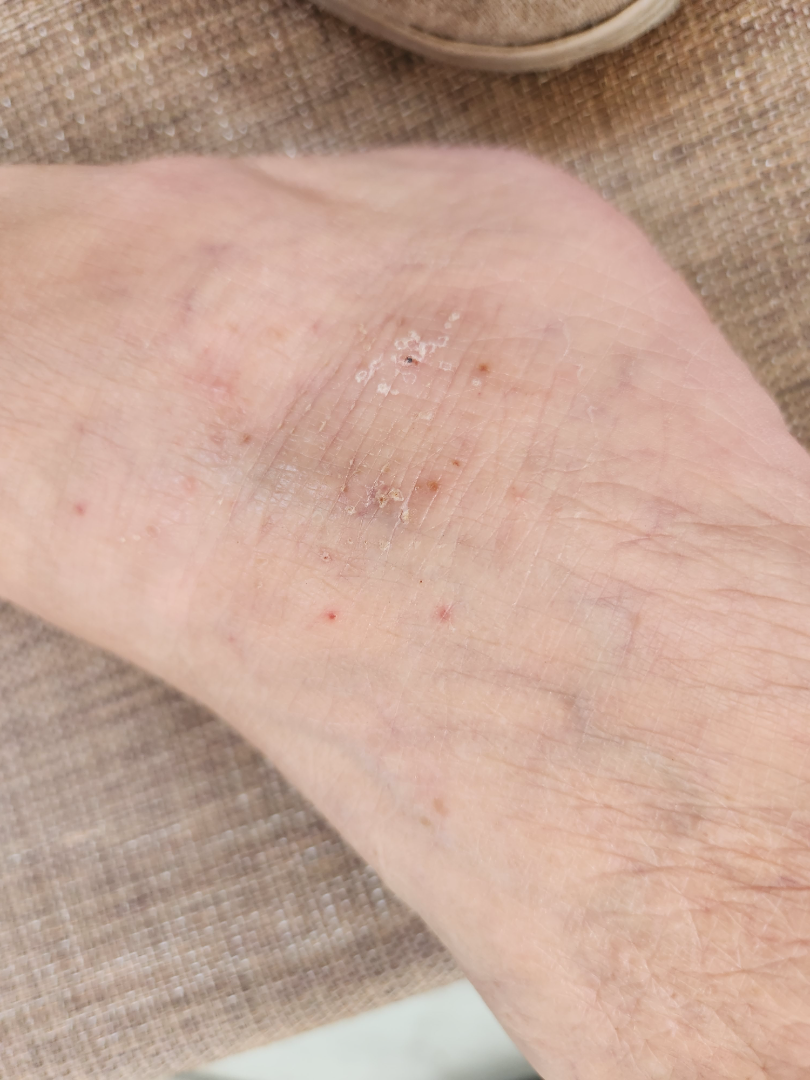Q: What conditions are considered?
A: most likely Lichen Simplex Chronicus; possibly Eczema; less likely is Psoriasis